A skin lesion imaged with a dermatoscope.
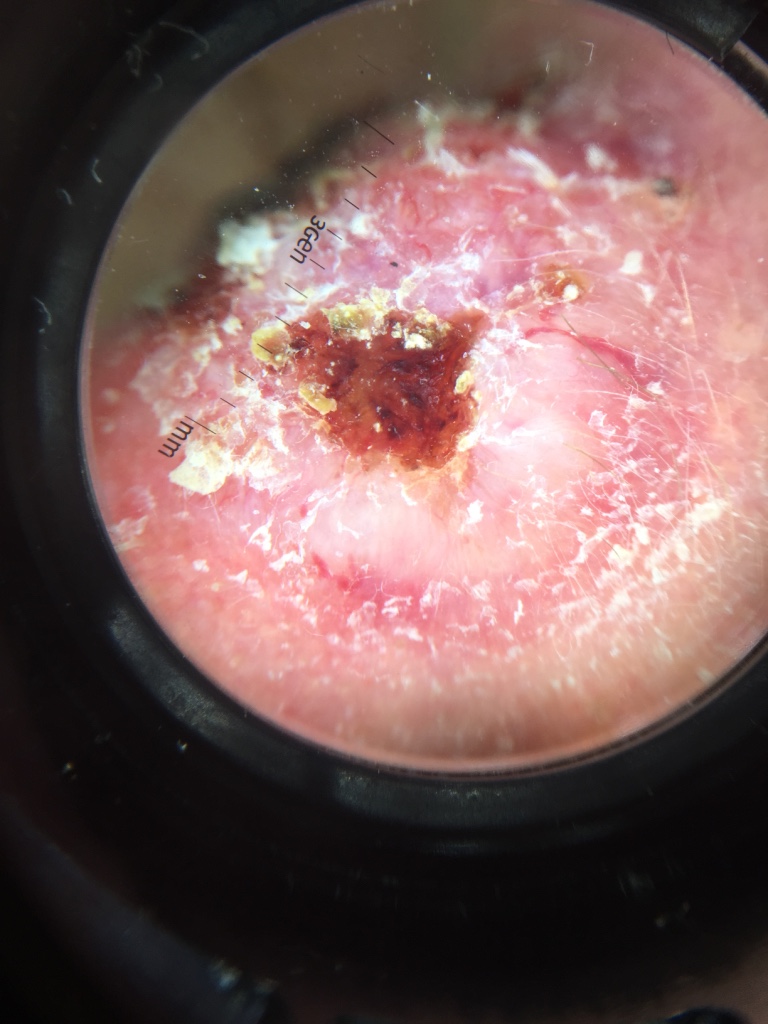classification: keratinocytic | label: basal cell carcinoma (biopsy-proven).